The subject is 40–49, male; this image was taken at an angle; the back of the hand is involved — 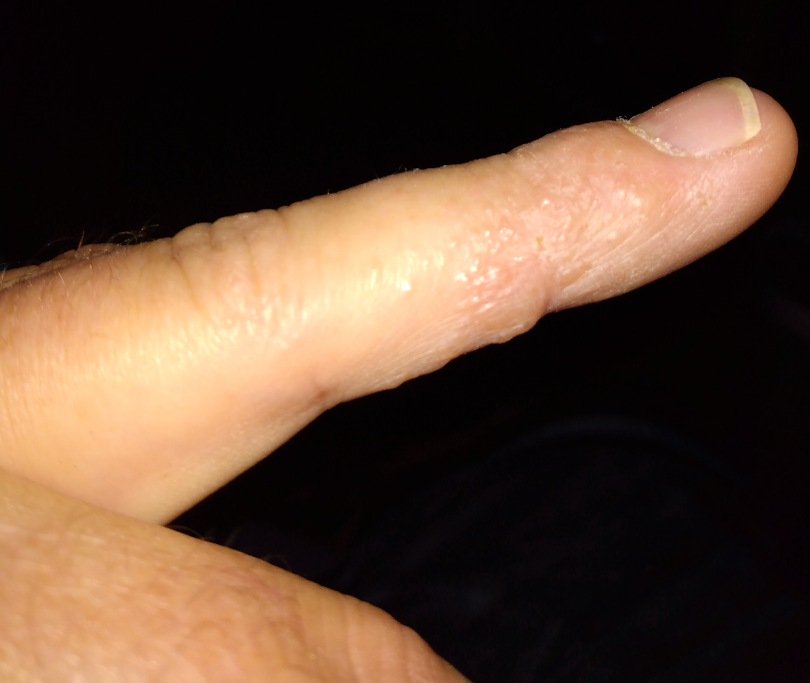Q: What is the differential diagnosis?
A: Eczema (weight 0.67); Allergic Contact Dermatitis (weight 0.33)